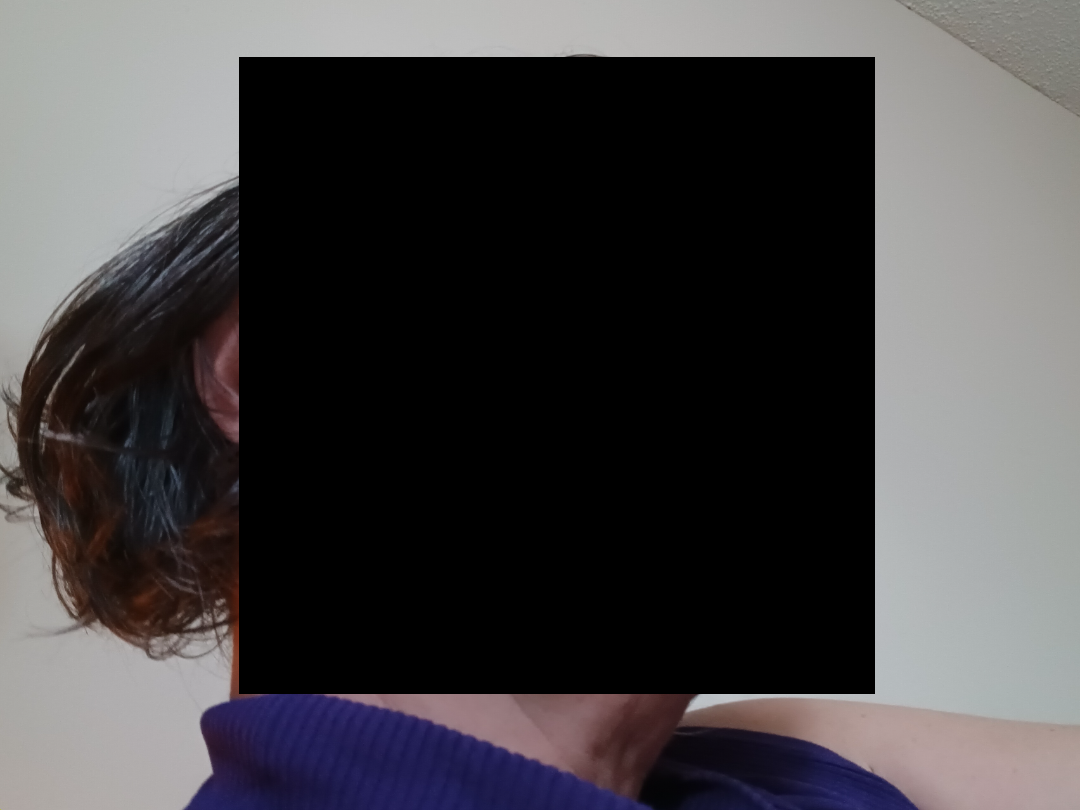The patient is a female aged 40–49. Self-categorized by the patient as a rash. The lesion is associated with pain, itching, darkening, bothersome appearance, enlargement and burning. The photograph was taken at an angle. Reported duration is more than five years. The patient indicates associated joint pain, mouth sores and fatigue.